This image was taken at an angle.
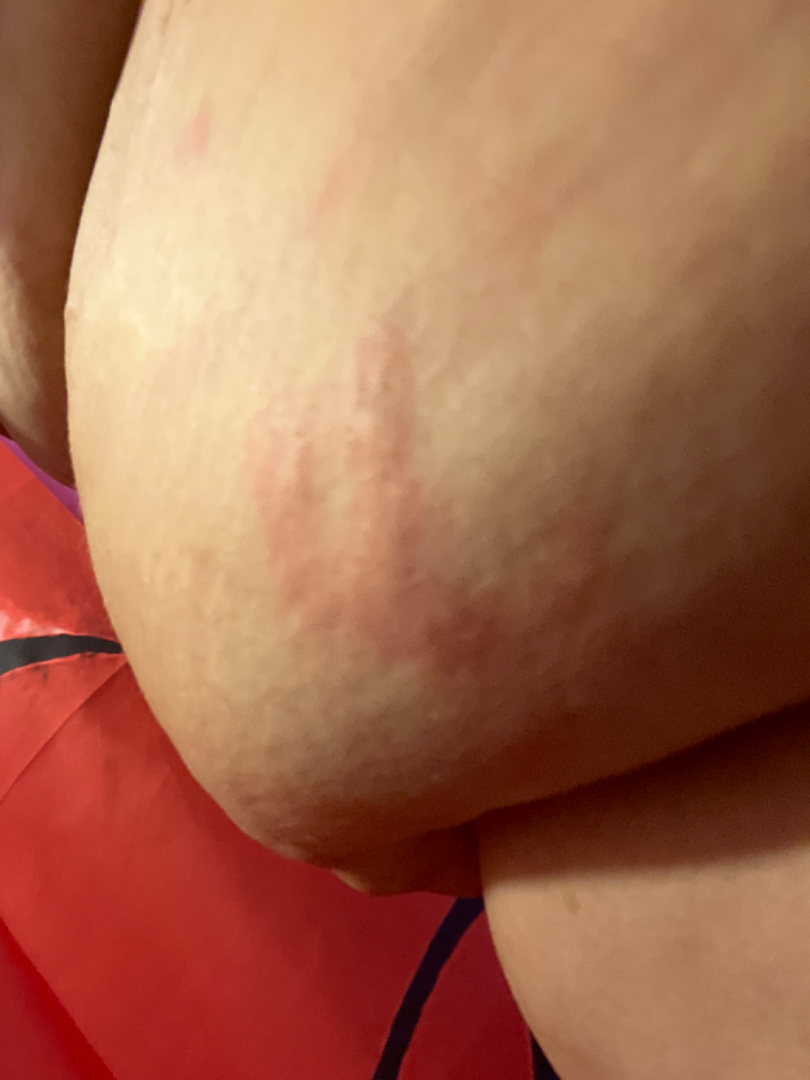Assessment:
The reviewer was unable to grade this case for skin condition.
Clinical context:
Reported lesion symptoms include burning. FST III.